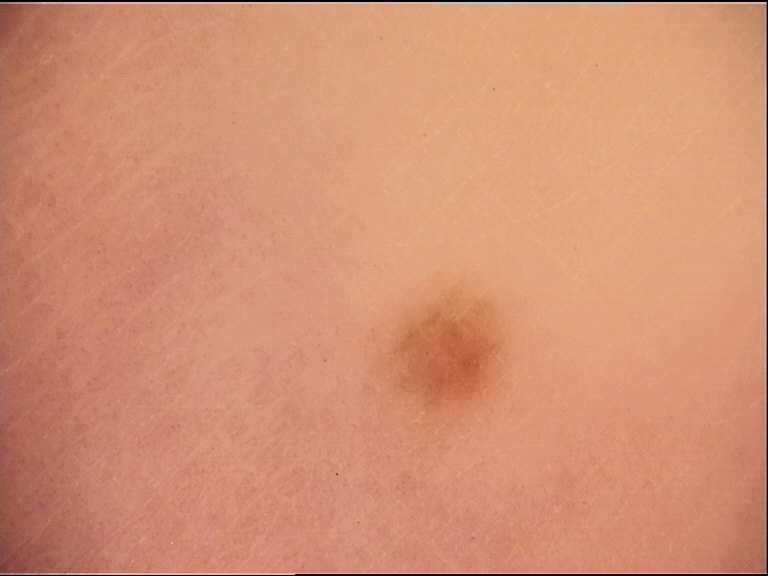– image: dermatoscopy
– classification: banal
– diagnosis: junctional nevus (expert consensus)